This is a close-up image; the leg and top or side of the foot are involved — 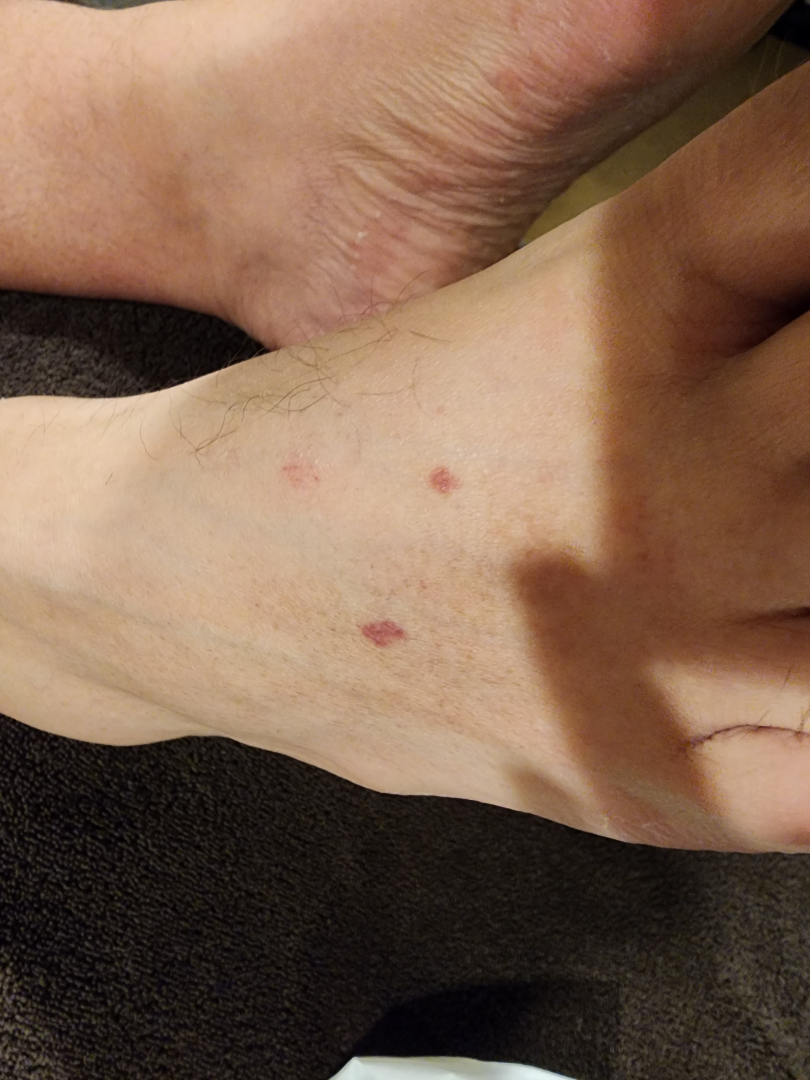Assessment:
The reviewing dermatologist's impression was: Pigmented purpuric eruption and Leukocytoclastic Vasculitis were considered with similar weight.